A dermoscopic image of a skin lesion: 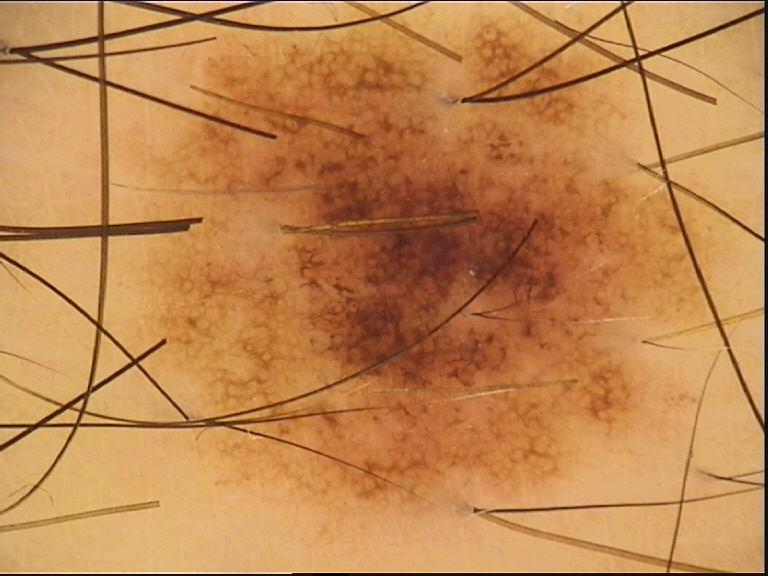Consistent with a dysplastic junctional nevus.